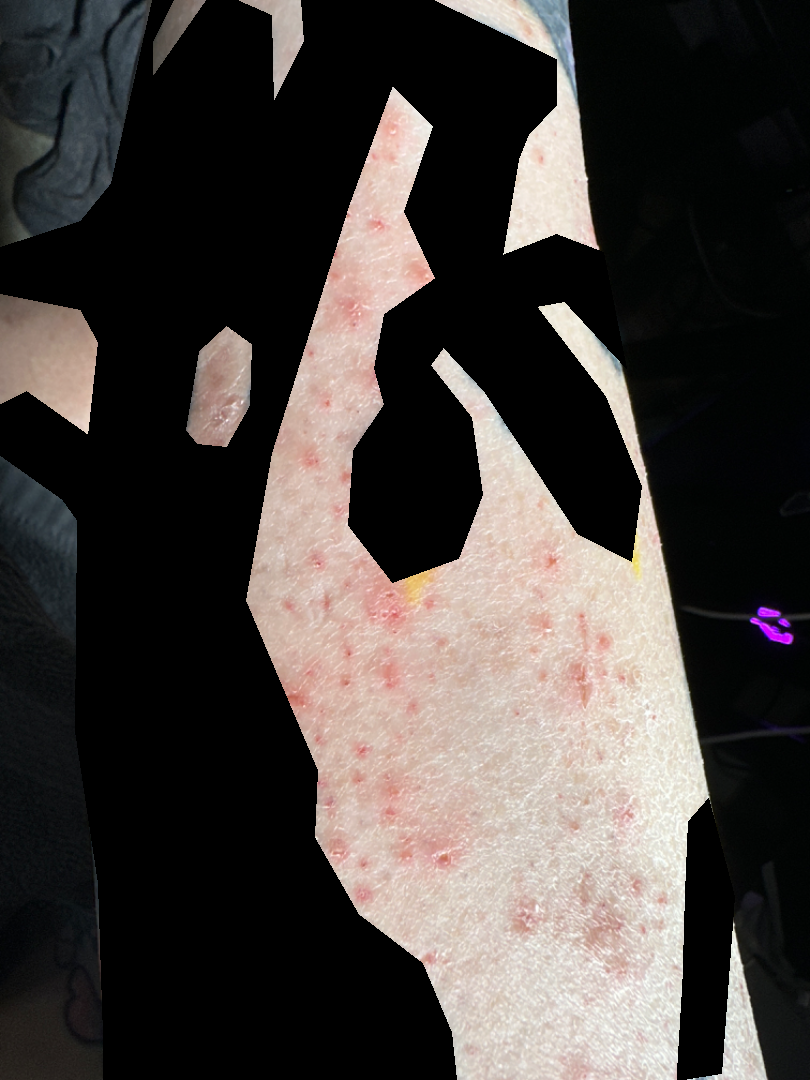<report>
<patient_category>a rash</patient_category>
<duration>about one day</duration>
<symptoms>none reported</symptoms>
<shot_type>close-up</shot_type>
<texture>raised or bumpy</texture>
<patient>female, age 40–49</patient>
<body_site>leg</body_site>
<differential>
  <leading>Pigmented purpuric eruption</leading>
  <considered>Leukocytoclastic Vasculitis</considered>
</differential>
</report>